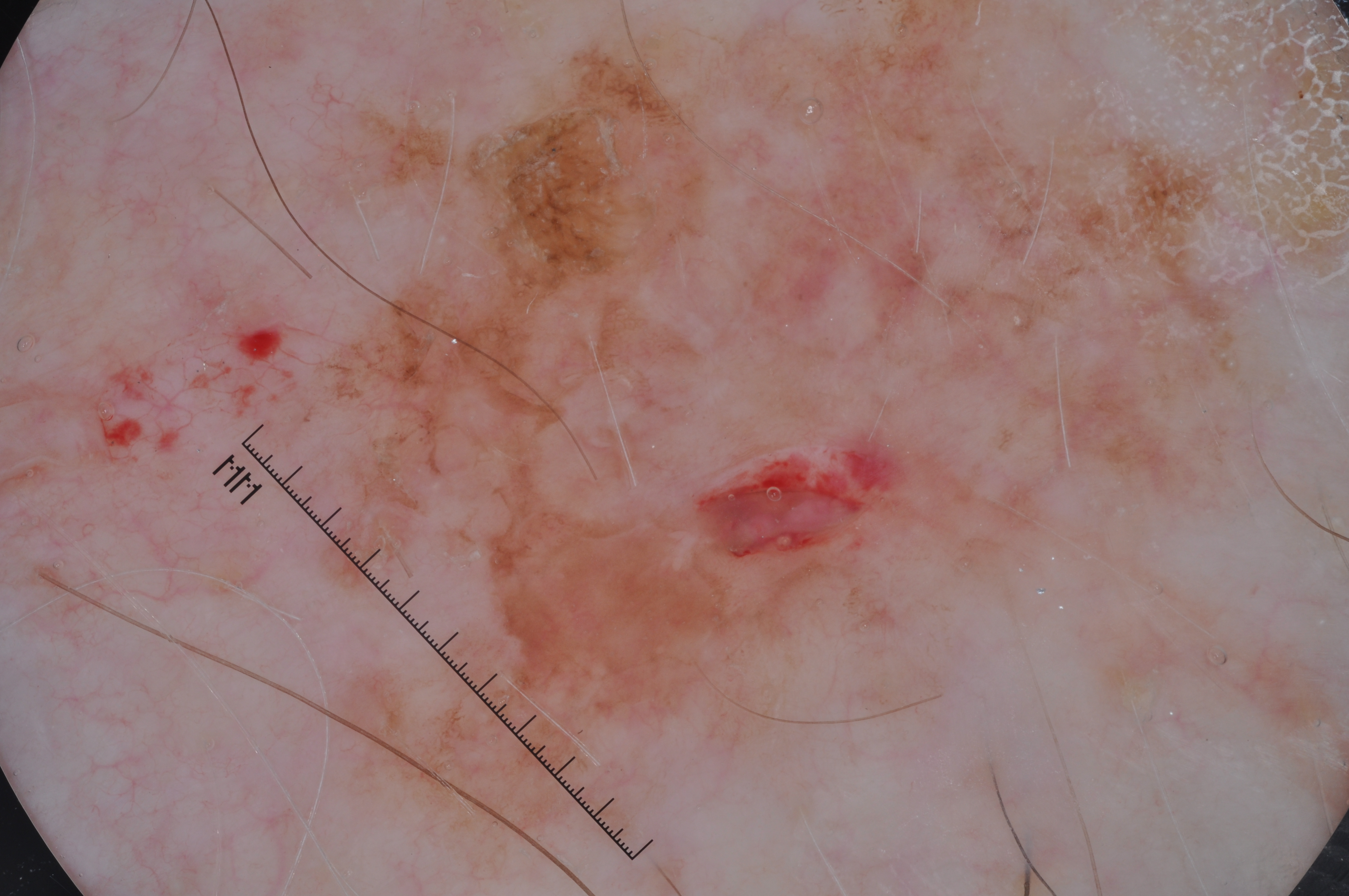Q: What are the patient's age and sex?
A: male, aged 83 or older
Q: What is the imaging modality?
A: dermoscopy
Q: What dermoscopic features are present?
A: pigment network and milia-like cysts; absent: streaks and negative network
Q: What is the lesion's bounding box?
A: 271, 2, 1254, 870
Q: How large is the lesion within the image?
A: ~53% of the field
Q: What did the assessment conclude?
A: a melanoma